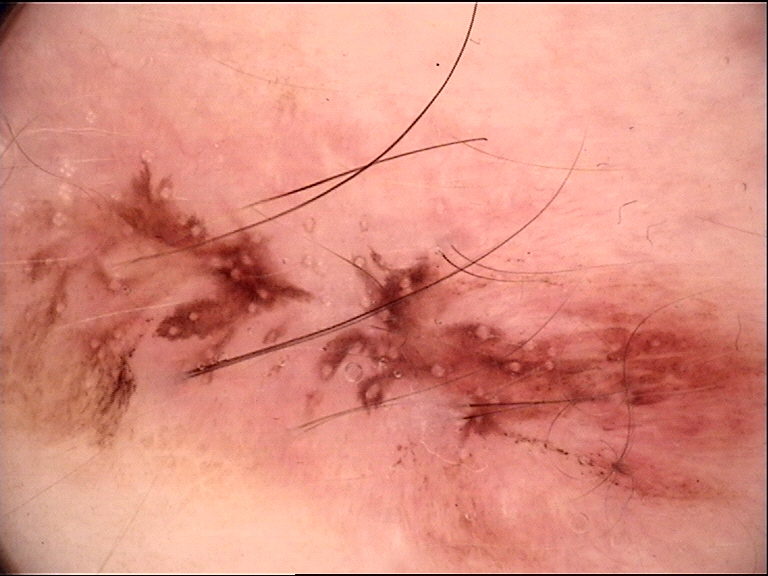Findings:
A dermoscopy image of a single skin lesion. This is a dysplastic lesion.
Impression:
Diagnosed as a benign lesion — a recurrent nevus.